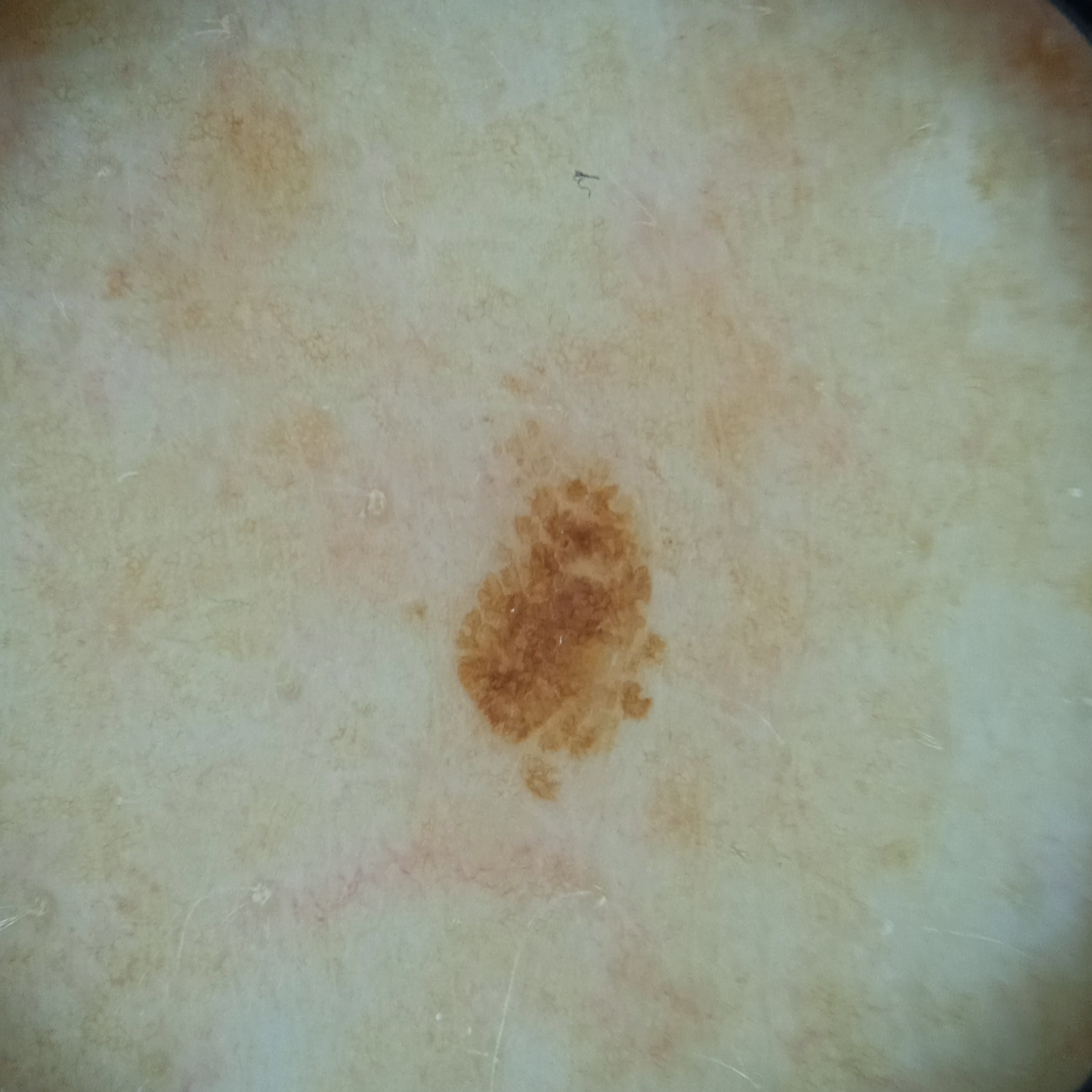Q: What was the diagnosis?
A: seborrheic keratosis (dermatologist consensus)